A clinical close-up of a skin lesion · by self-report, a personal history of skin cancer · a female subject 50 years old · the patient says their skin reddens with sun exposure · a moderate number of moles by the patient's own estimate · acquired for a research image collection, with no referral diagnosis.
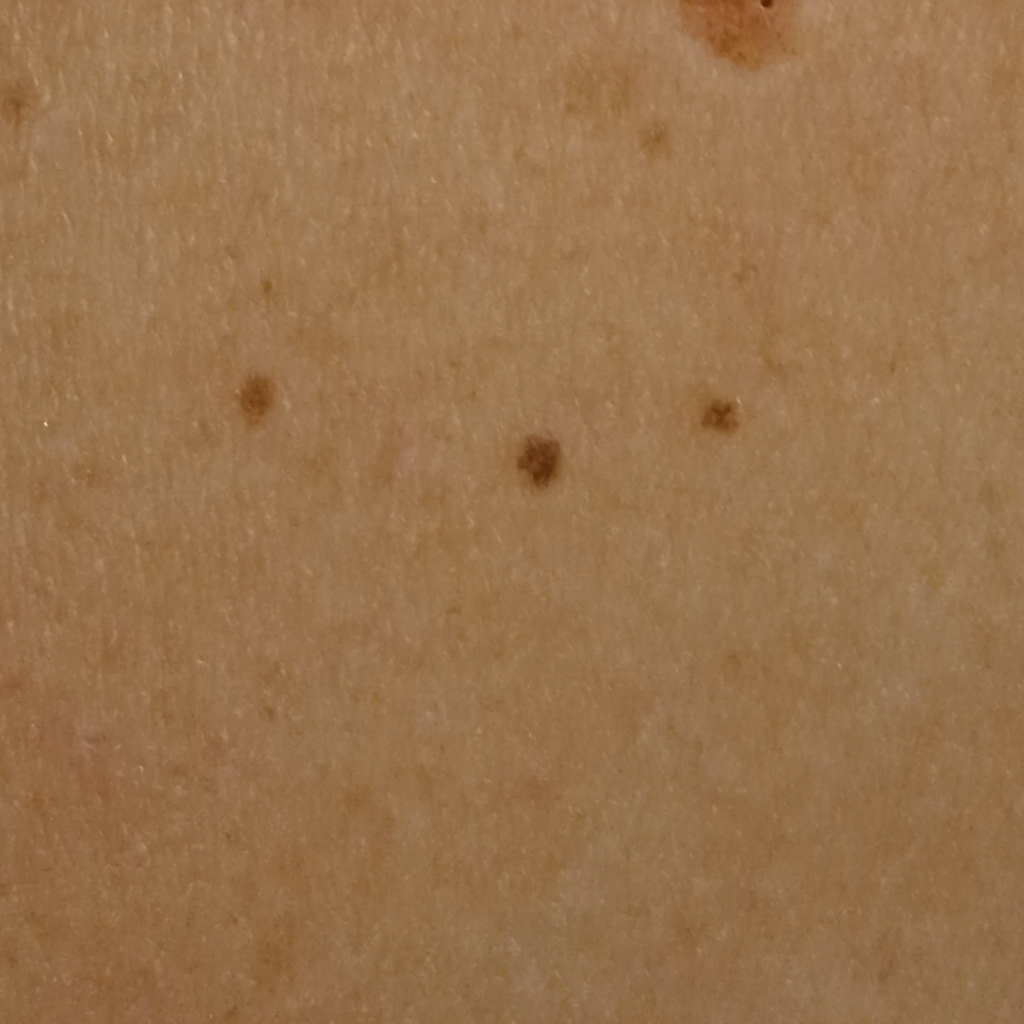body site: an arm | diameter: 2.5 mm | assessment: melanocytic nevus (dermatologist consensus).